Dermoscopy of a skin lesion.
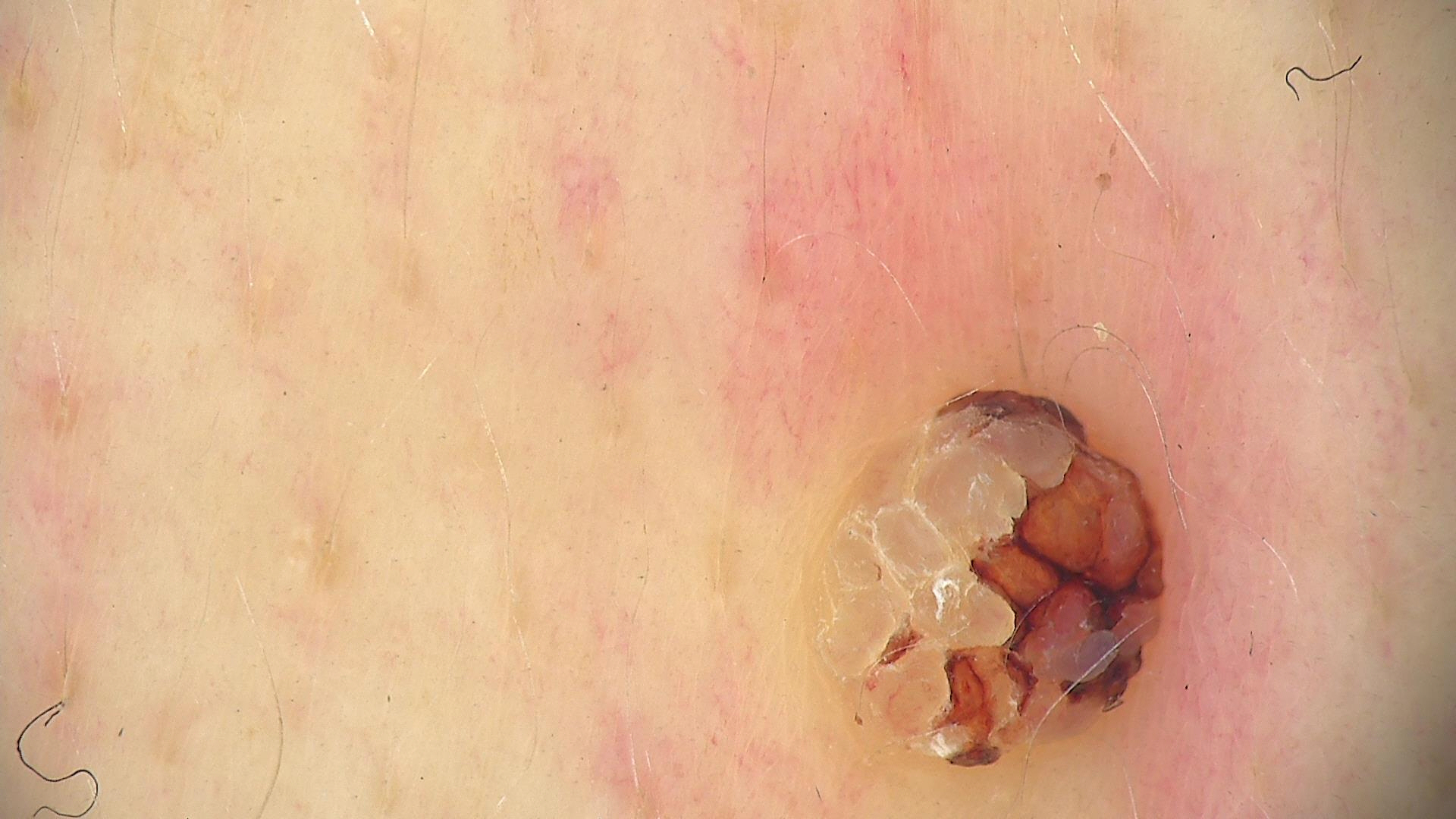<case>
  <lesion_type>
    <main_class>keratinocytic</main_class>
  </lesion_type>
  <diagnosis>
    <name>seborrheic keratosis</name>
    <code>sk</code>
    <malignancy>benign</malignancy>
    <super_class>non-melanocytic</super_class>
    <confirmation>expert consensus</confirmation>
  </diagnosis>
</case>